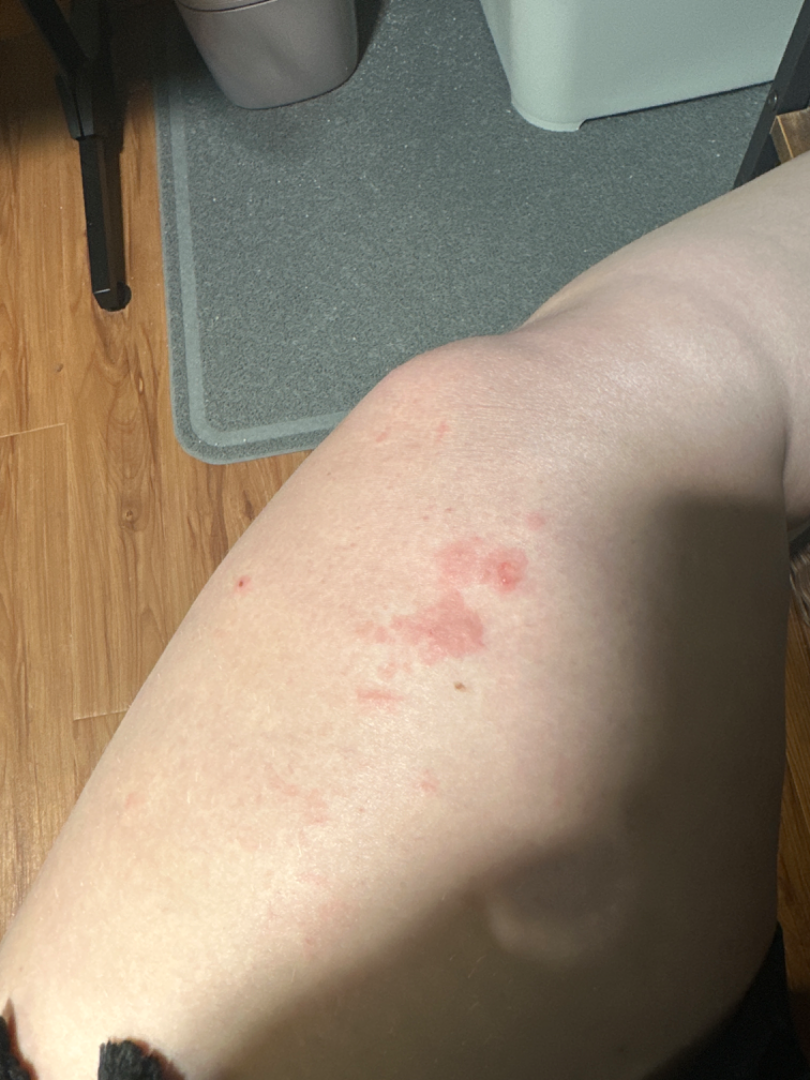Notes:
• patient-reported symptoms: itching, enlargement and burning
• shot type: close-up
• body site: leg
• described texture: raised or bumpy and fluid-filled
• duration: less than one week
• impression: Acute dermatitis, NOS (favored)